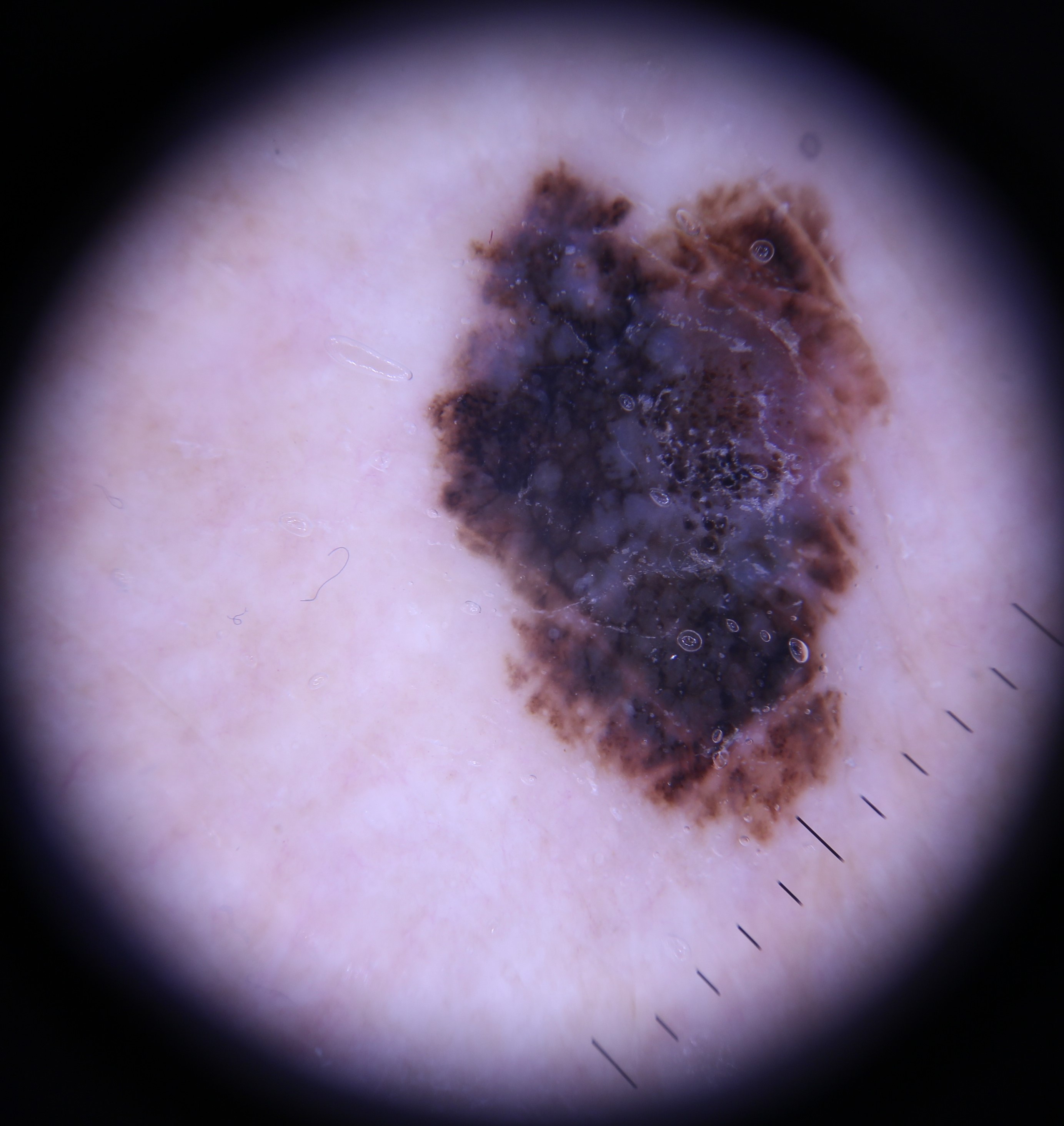A dermoscopic photograph of a skin lesion.
The biopsy diagnosis was a malignancy — a melanoma.